The subject is male. The arm and back of the hand are involved. The photograph is a close-up of the affected area — 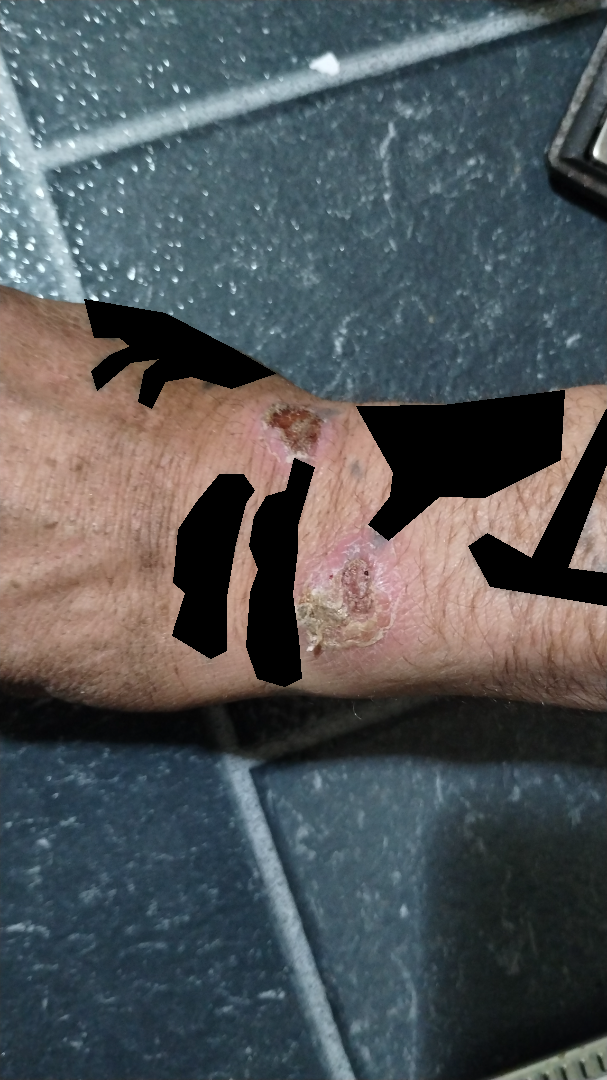The reviewer was unable to grade this case for skin condition.